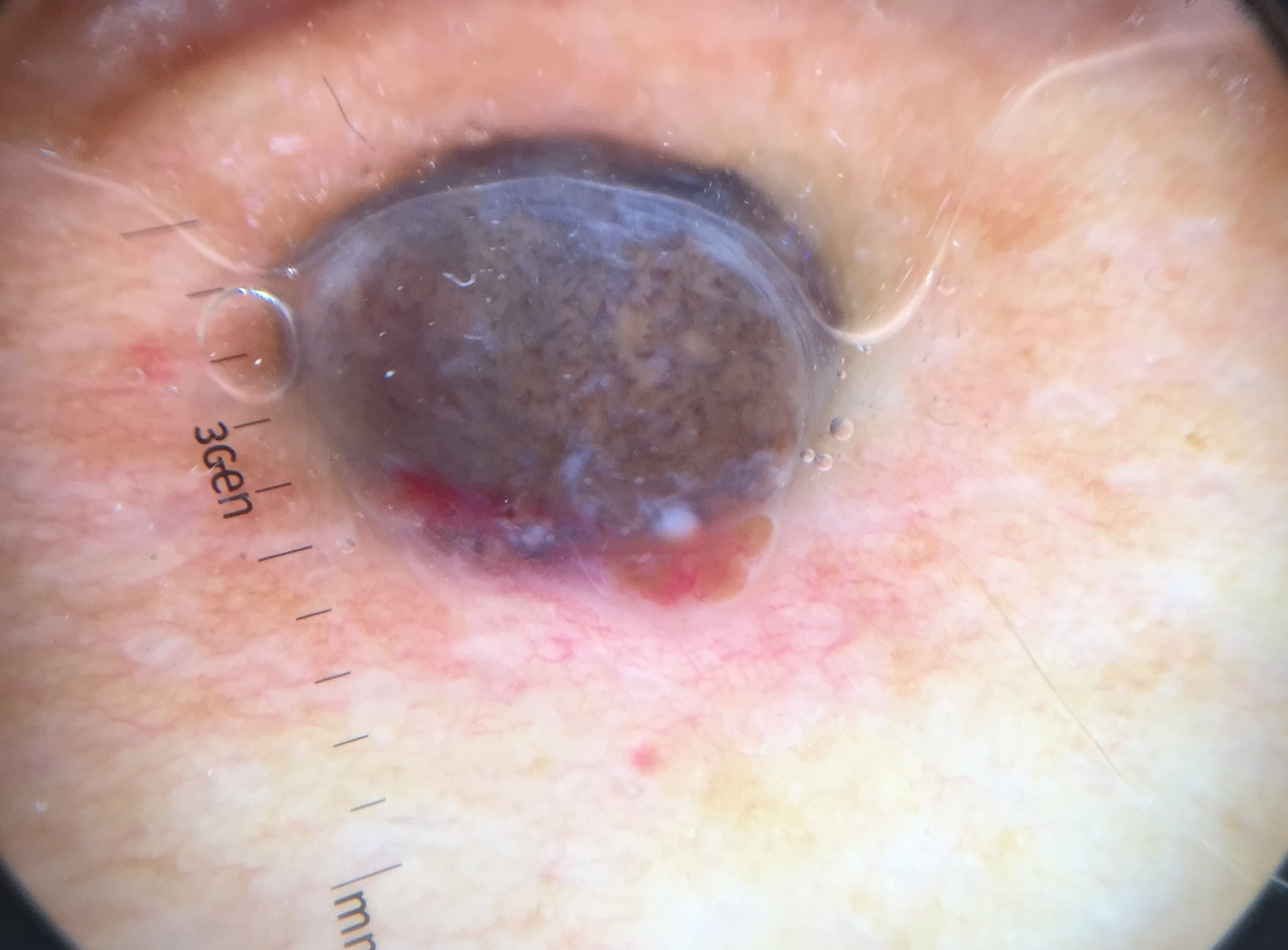pathology: melanoma (biopsy-proven)